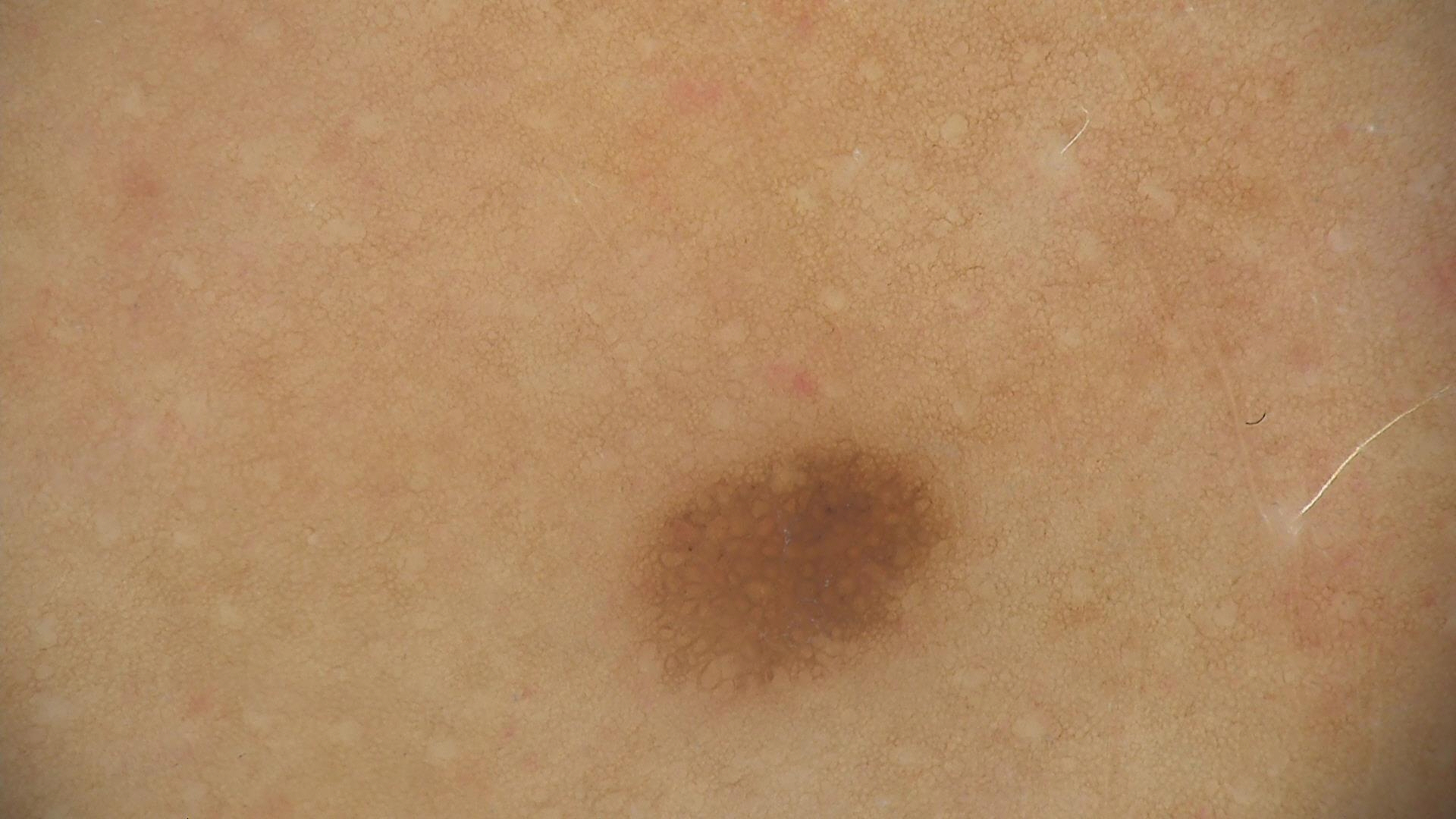Diagnosed as a junctional nevus.